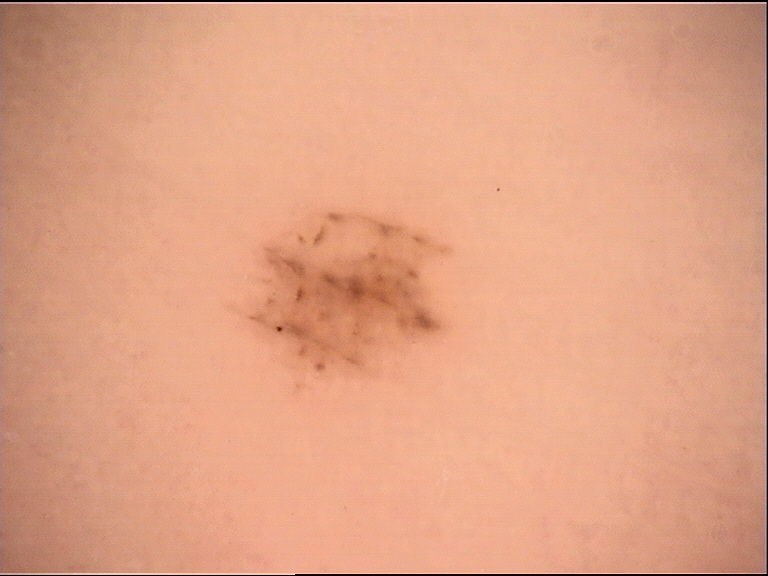Q: What kind of image is this?
A: dermoscopy
Q: What is this lesion?
A: acral dysplastic junctional nevus (expert consensus)